Female patient, age 18–29; the patient reports darkening, bleeding, bothersome appearance, burning and itching; this image was taken at an angle; the lesion is described as flat; the lesion involves the front of the torso, arm, back of the hand, back of the torso and leg.
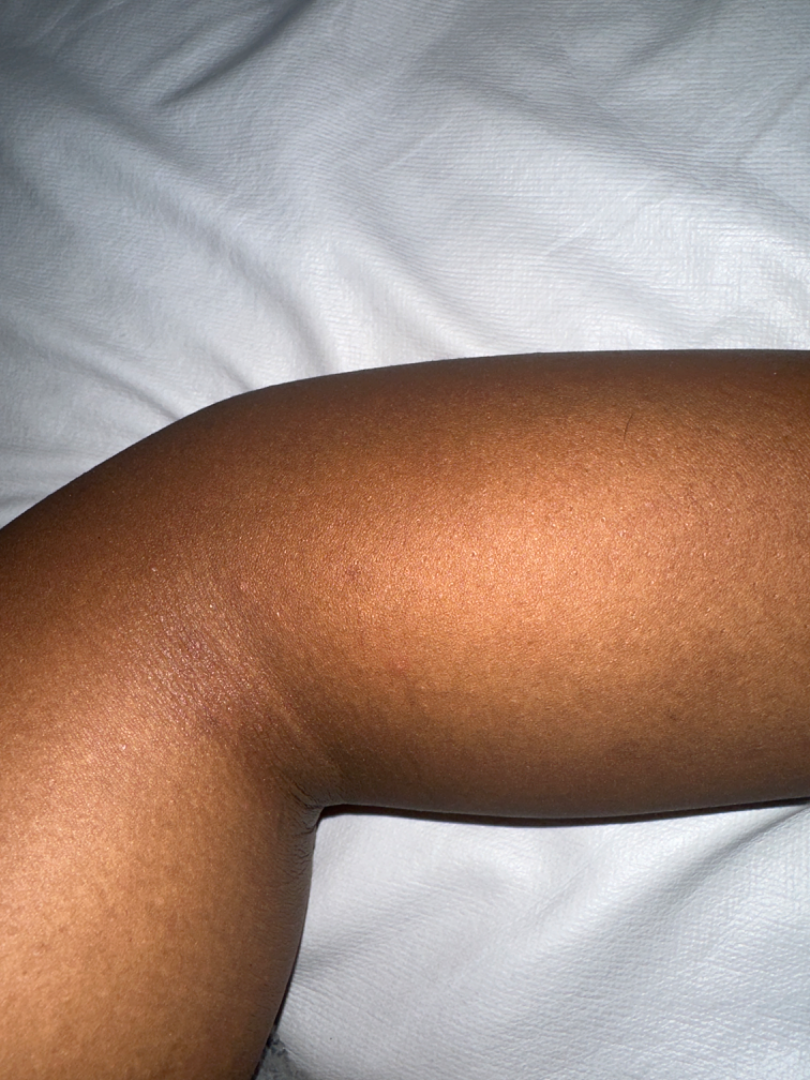The dermatologist could not determine a likely condition from the photograph alone.